The photograph was taken at an angle: 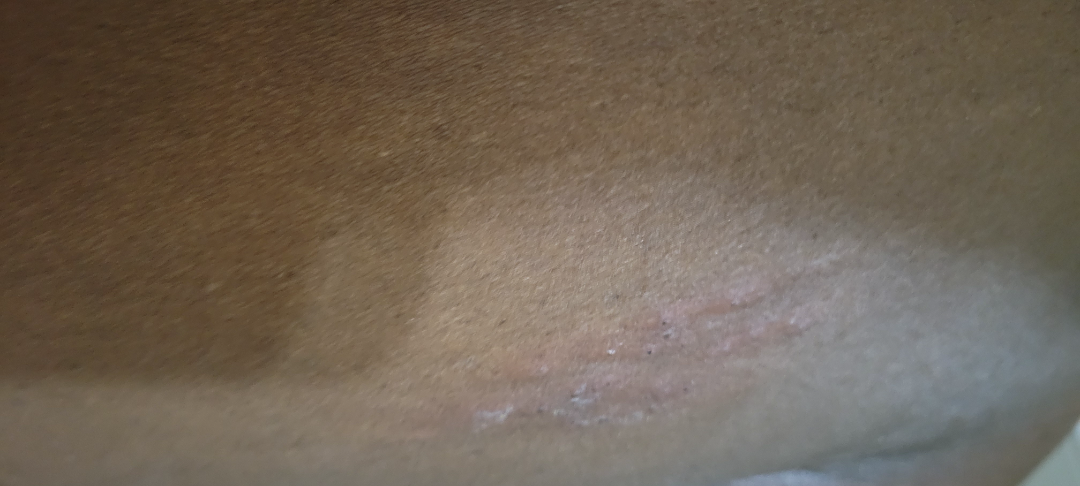Q: What was the assessment?
A: not assessable
Q: Texture?
A: raised or bumpy
Q: How long has this been present?
A: less than one week
Q: Reported symptoms?
A: pain and bothersome appearance
Q: Fitzpatrick or Monk tone?
A: human graders estimated MST 7 (US pool) or 4 (India pool)
Q: Constitutional symptoms?
A: none reported